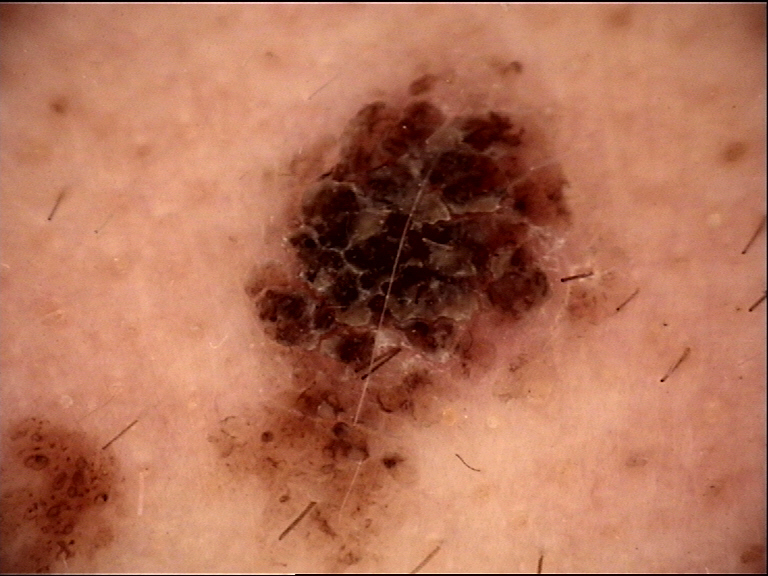assessment: congenital compound nevus (expert consensus).